A male patient age 15. A skin lesion imaged with a dermatoscope. Referred with a clinical suspicion of melanocytic nevus.
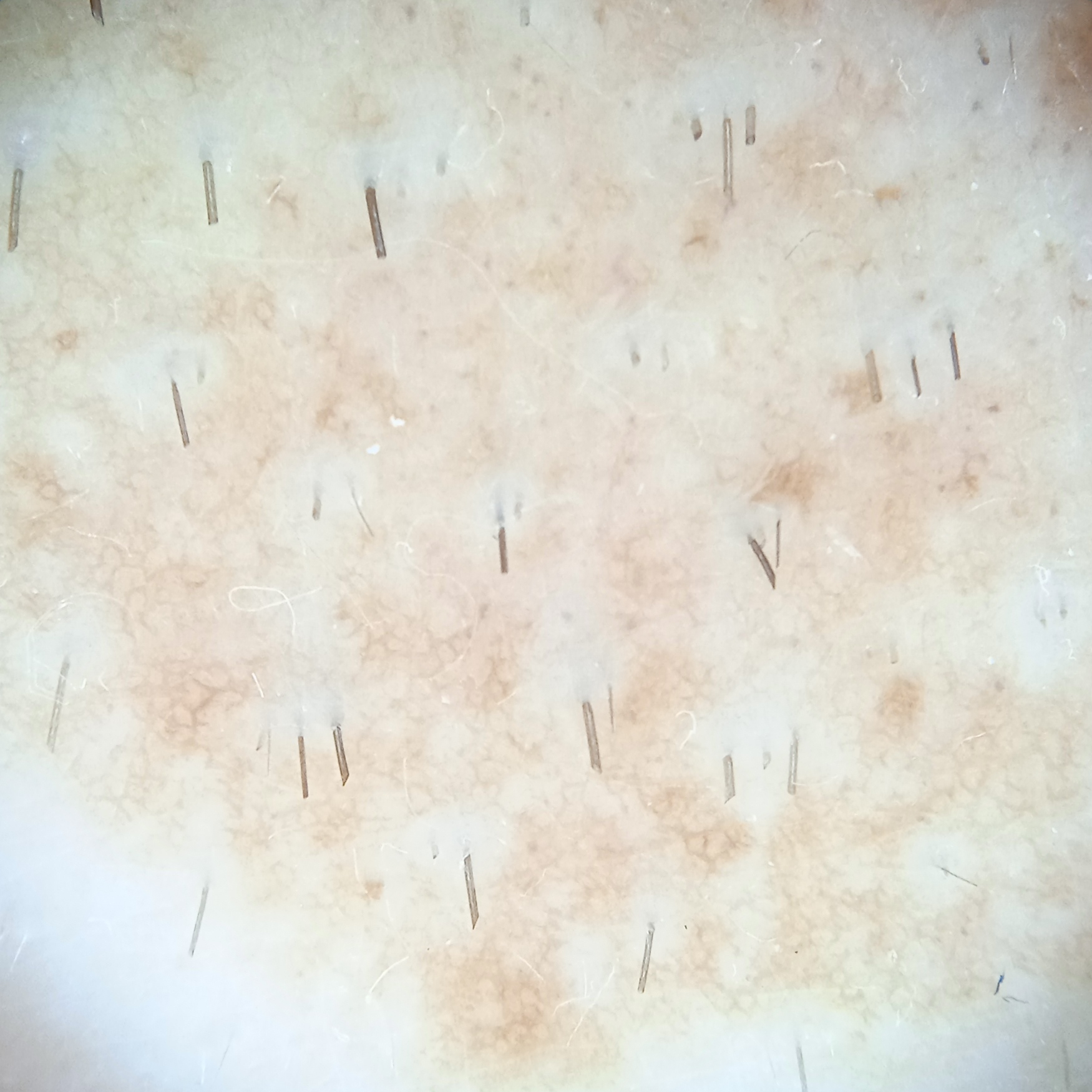Located on an arm. On biopsy, the diagnosis was a melanocytic nevus, following a punch biopsy.